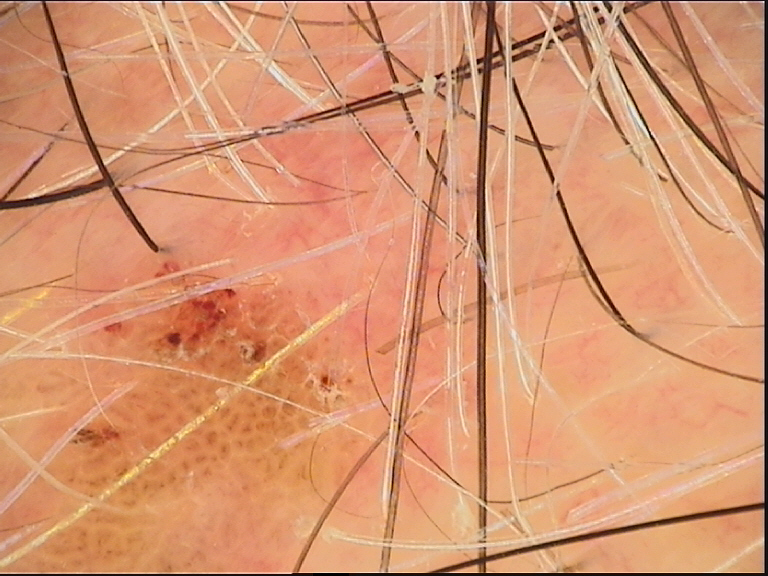imaging — dermatoscopy; lesion type — keratinocytic; diagnostic label — seborrheic keratosis (expert consensus).